This is a dermoscopic photograph of a skin lesion. A male subject in their mid-50s:
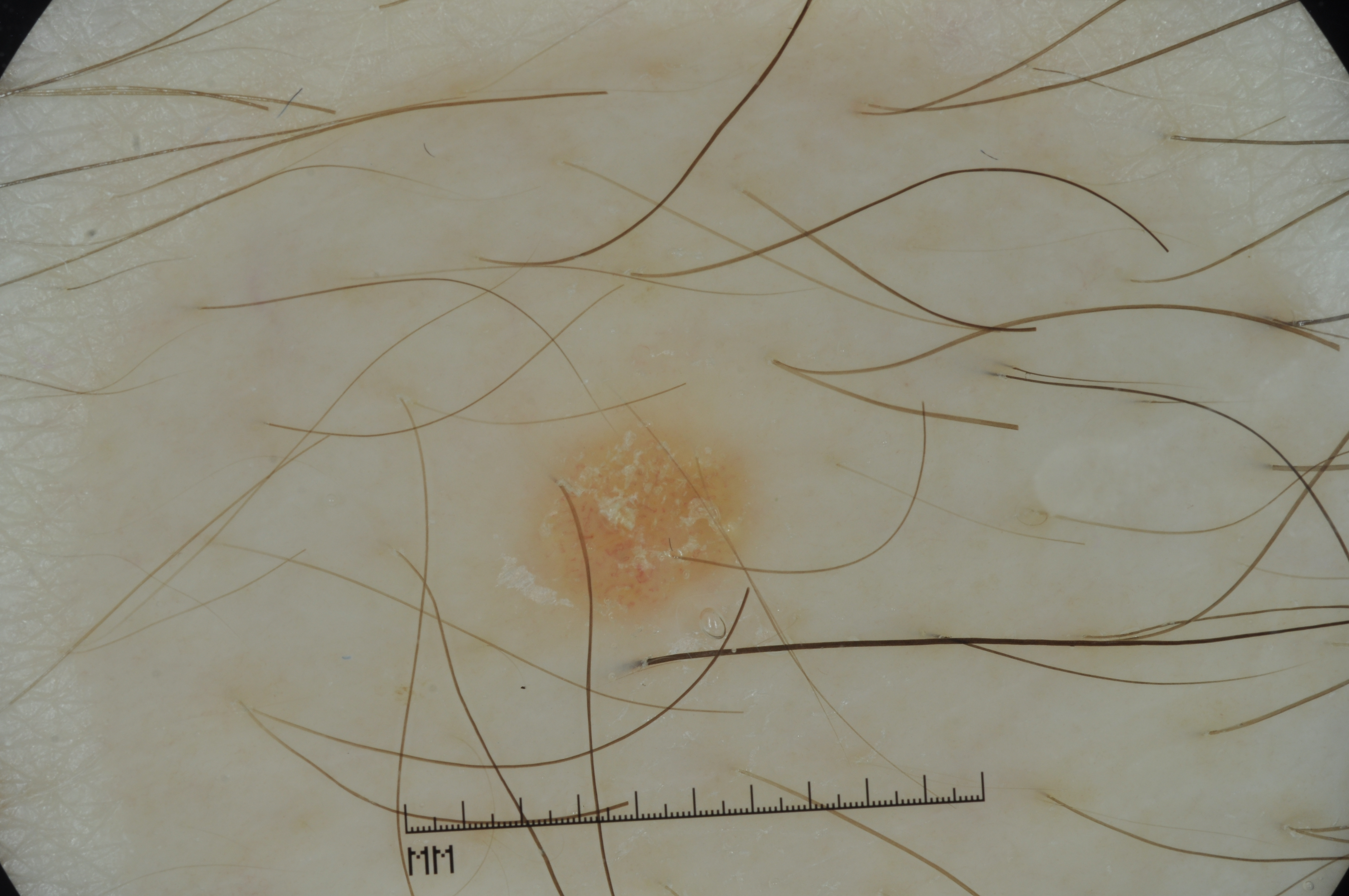<case>
<dermoscopic_features>
  <present>milia-like cysts</present>
  <absent>pigment network, negative network, streaks</absent>
</dermoscopic_features>
<lesion_location>
  <bbox_xyxy>519, 406, 758, 627</bbox_xyxy>
</lesion_location>
<diagnosis>
  <name>seborrheic keratosis</name>
  <malignancy>benign</malignancy>
  <lineage>keratinocytic</lineage>
  <provenance>clinical</provenance>
</diagnosis>
</case>